A close-up photograph — 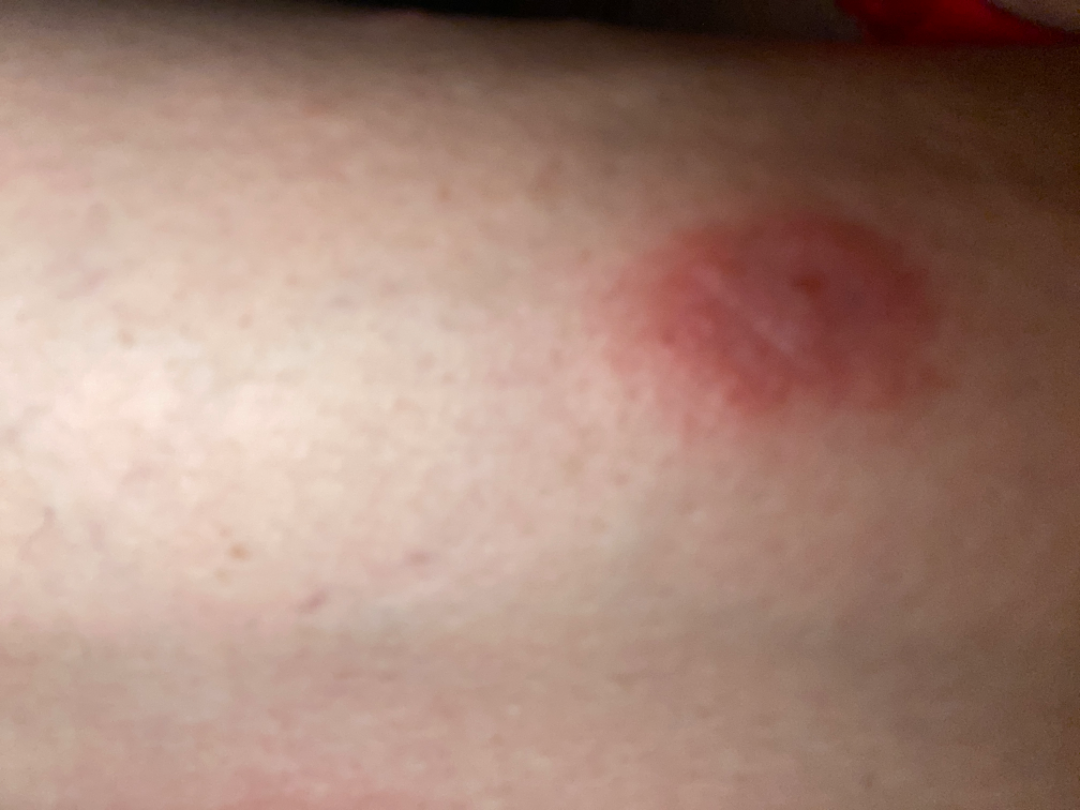Notes:
* assessment: unable to determine
* patient's own categorization: a rash
* texture: rough or flaky and raised or bumpy